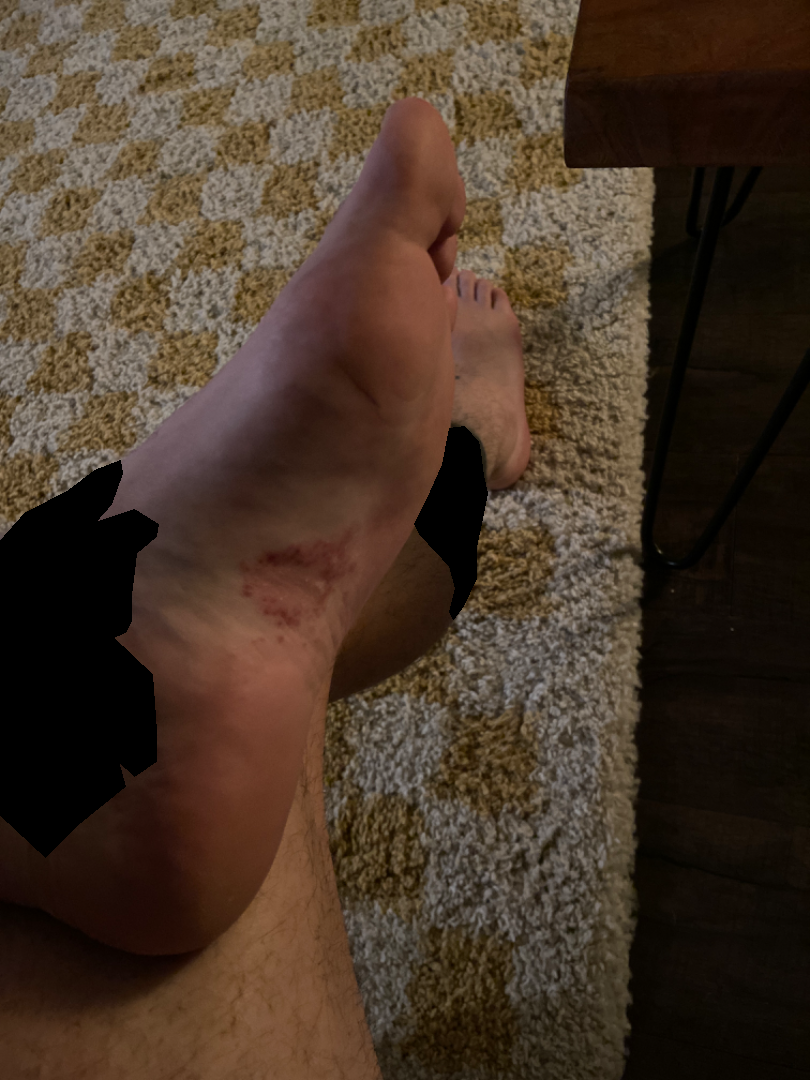Findings:
Most likely Psoriasis; also consider Tinea; a remote consideration is Allergic Contact Dermatitis.